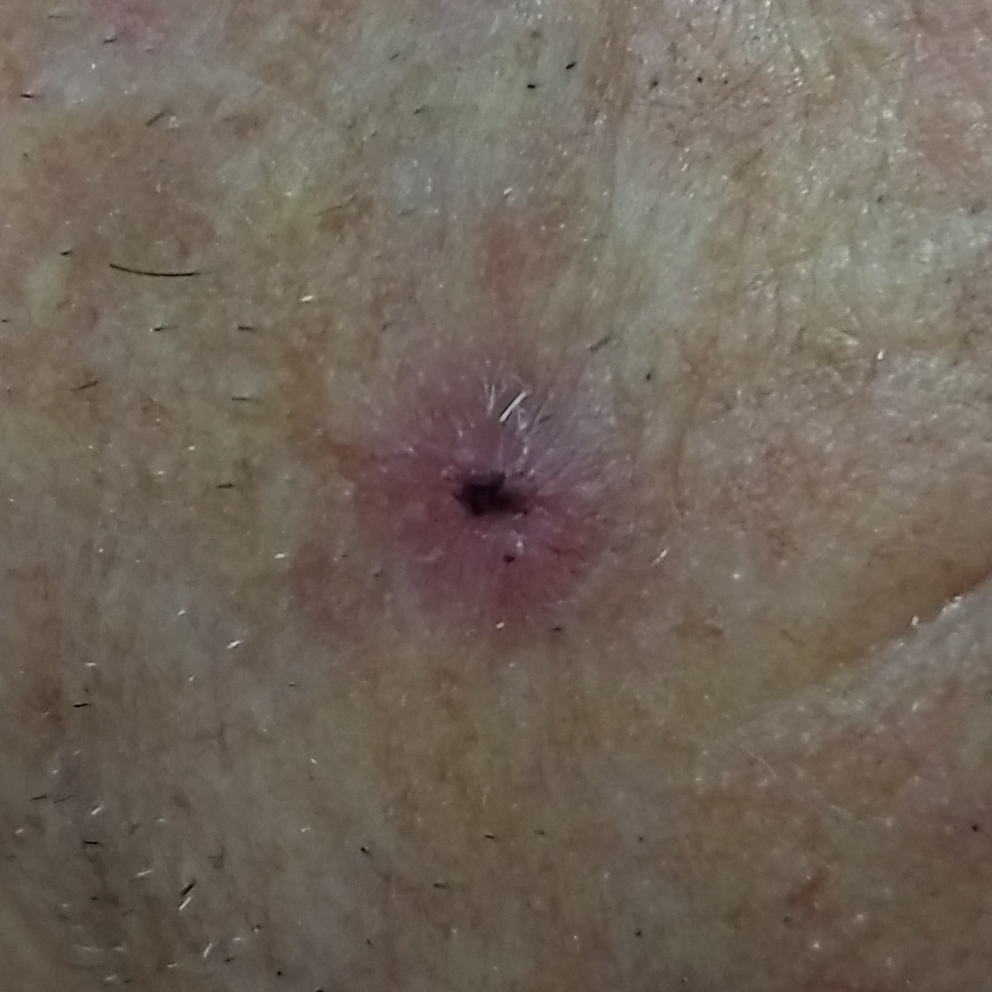Patient and lesion: A clinical photo of a skin lesion taken with a smartphone. The patient is Fitzpatrick phototype II. A male patient in their mid-80s. The chart notes tobacco use, prior malignancy (patient or family), no alcohol use, and no prior skin cancer (patient or family). The lesion is on the face. Pathology: The biopsy diagnosis was a malignancy — a basal cell carcinoma.